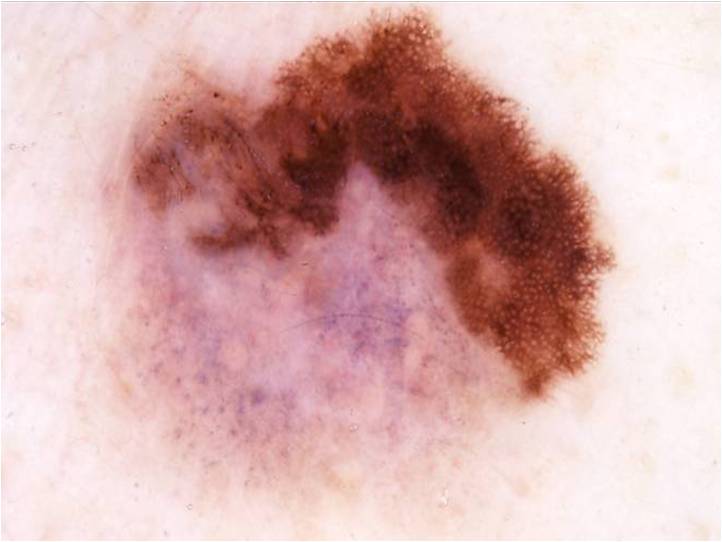Q: Patient demographics?
A: female, approximately 30 years of age
Q: What is the imaging modality?
A: dermatoscopic image of a skin lesion
Q: Which dermoscopic features were noted?
A: globules and pigment network
Q: What is the lesion's bounding box?
A: left=93, top=4, right=614, bottom=500
Q: What is the diagnosis?
A: a melanoma